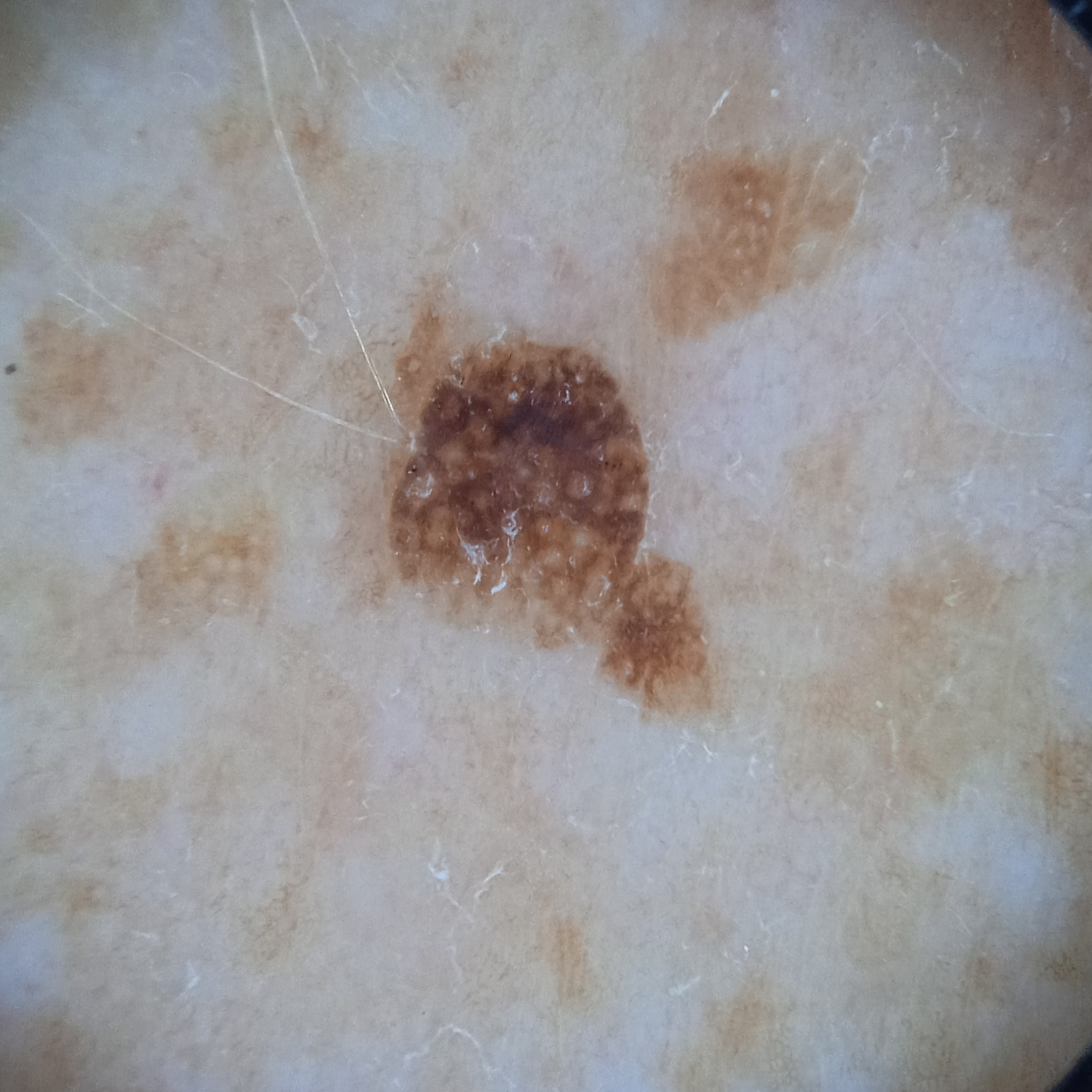Findings:
• subject · male, 73 years old
• referral context · research study (no referral diagnosis)
• image type · dermoscopy
• anatomic site · the back
• diameter · 5.5 mm
• diagnosis · seborrheic keratosis (dermatologist consensus)